A dermoscopic image of a skin lesion · collected as part of a research study, without a referral diagnosis · a female patient 54 years of age — 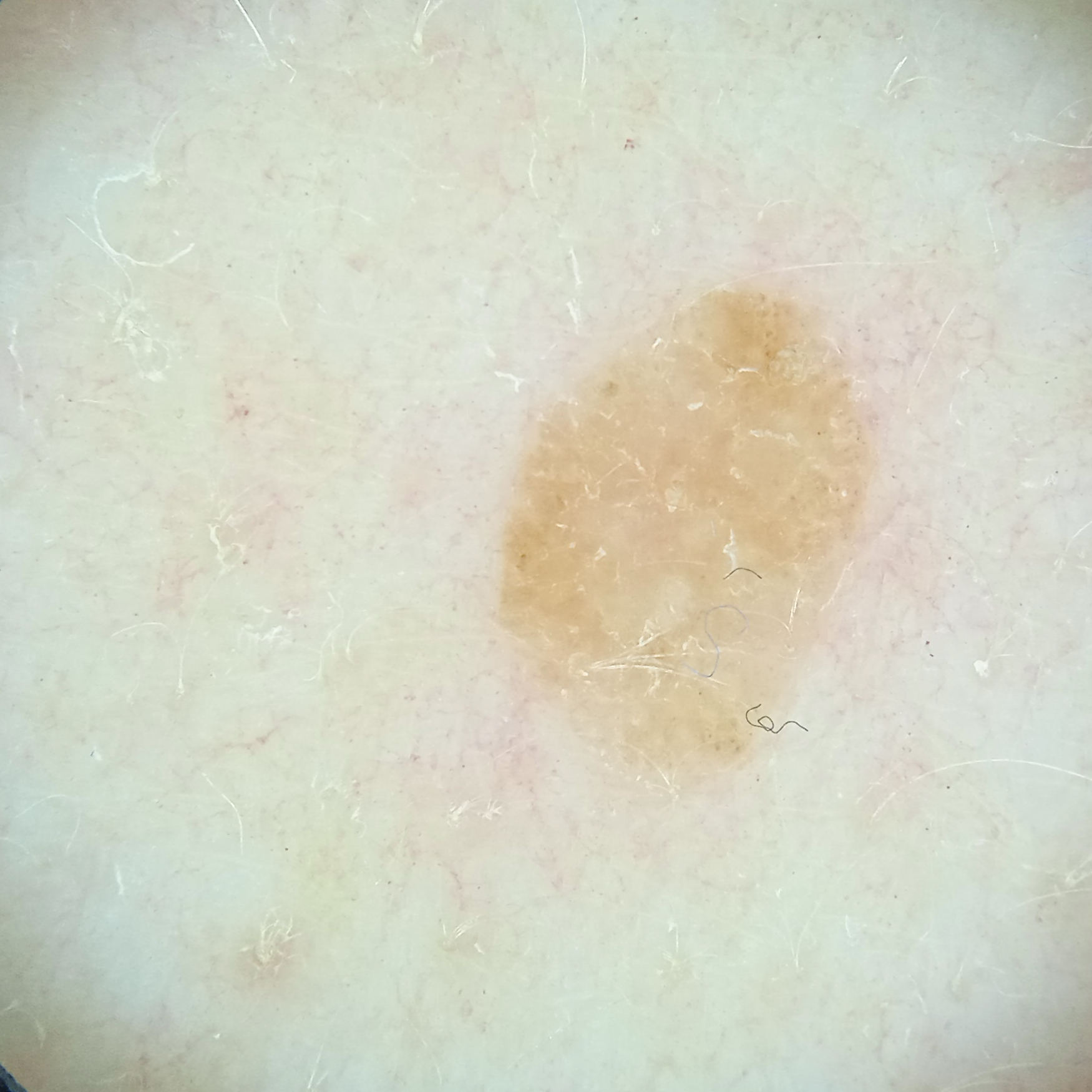<case>
<lesion_location>the back</lesion_location>
<lesion_size>
<diameter_mm>5.5</diameter_mm>
</lesion_size>
<diagnosis>
<name>seborrheic keratosis</name>
<malignancy>benign</malignancy>
</diagnosis>
</case>